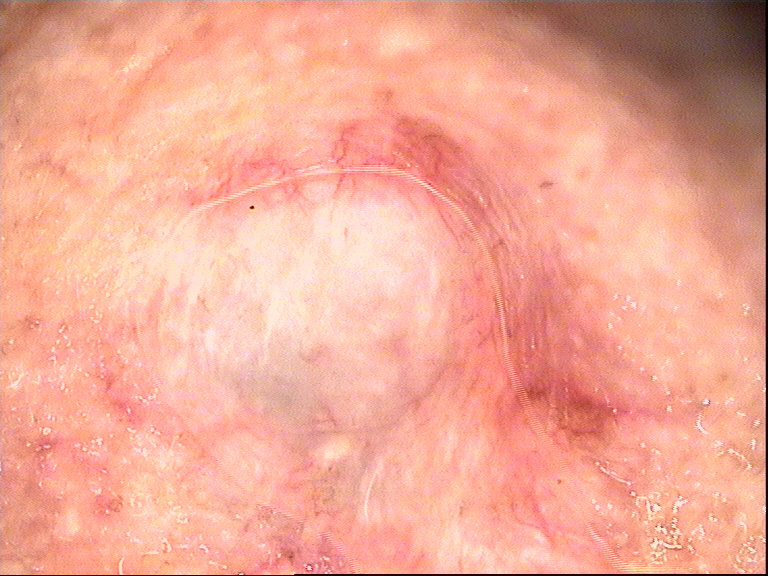A dermatoscopic image of a skin lesion.
The morphology is that of a keratinocytic lesion.
The biopsy diagnosis was a basal cell carcinoma.